On a questionnaire the patient reported a history of sunbed use; numerous moles by the patient's own estimate; dermoscopy of a skin lesion; the patient says their skin reddens with sun exposure; acquired for a research image collection, with no referral diagnosis — 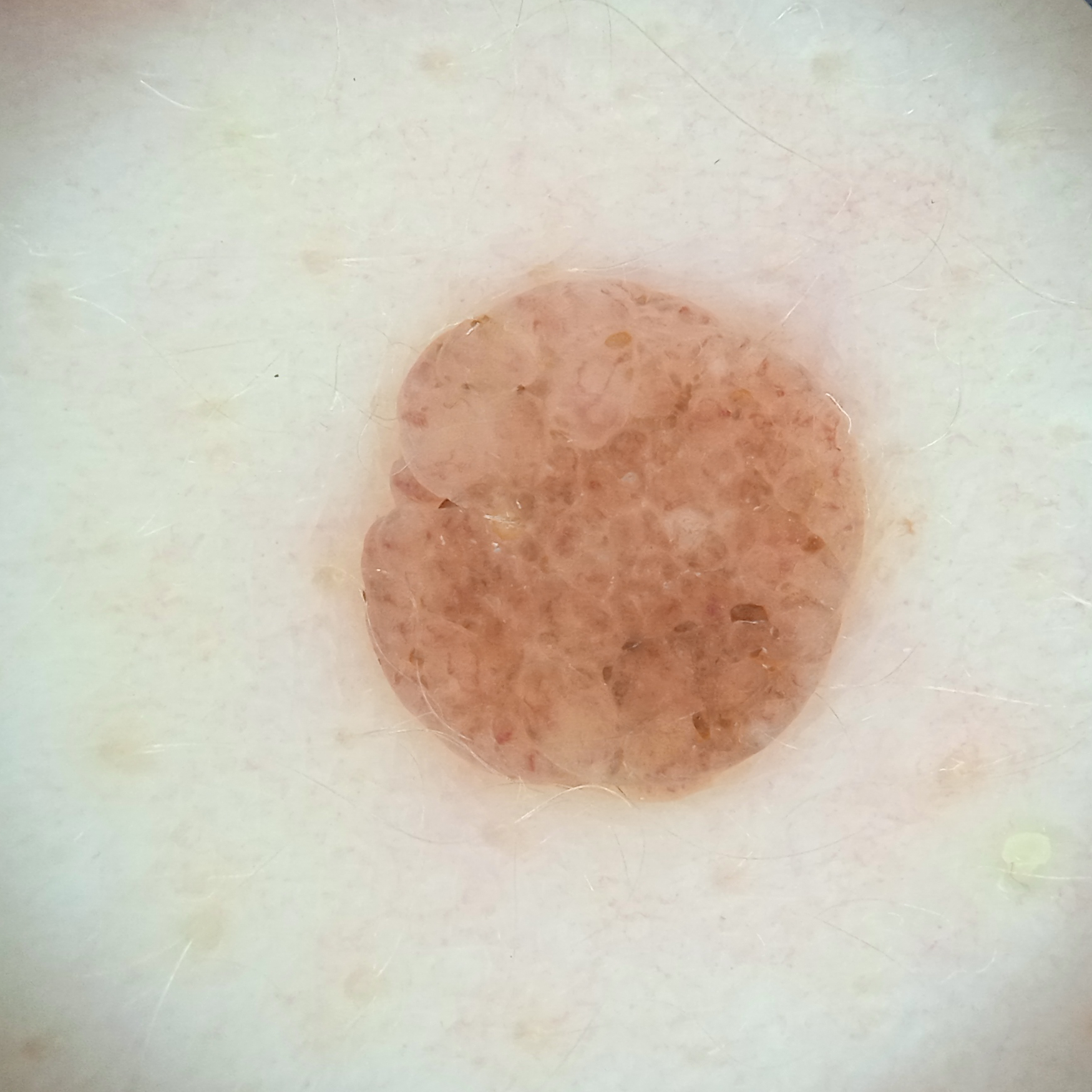location=the back | lesion size=5.6 mm | diagnosis=melanocytic nevus (dermatologist consensus).